An image taken at an angle: 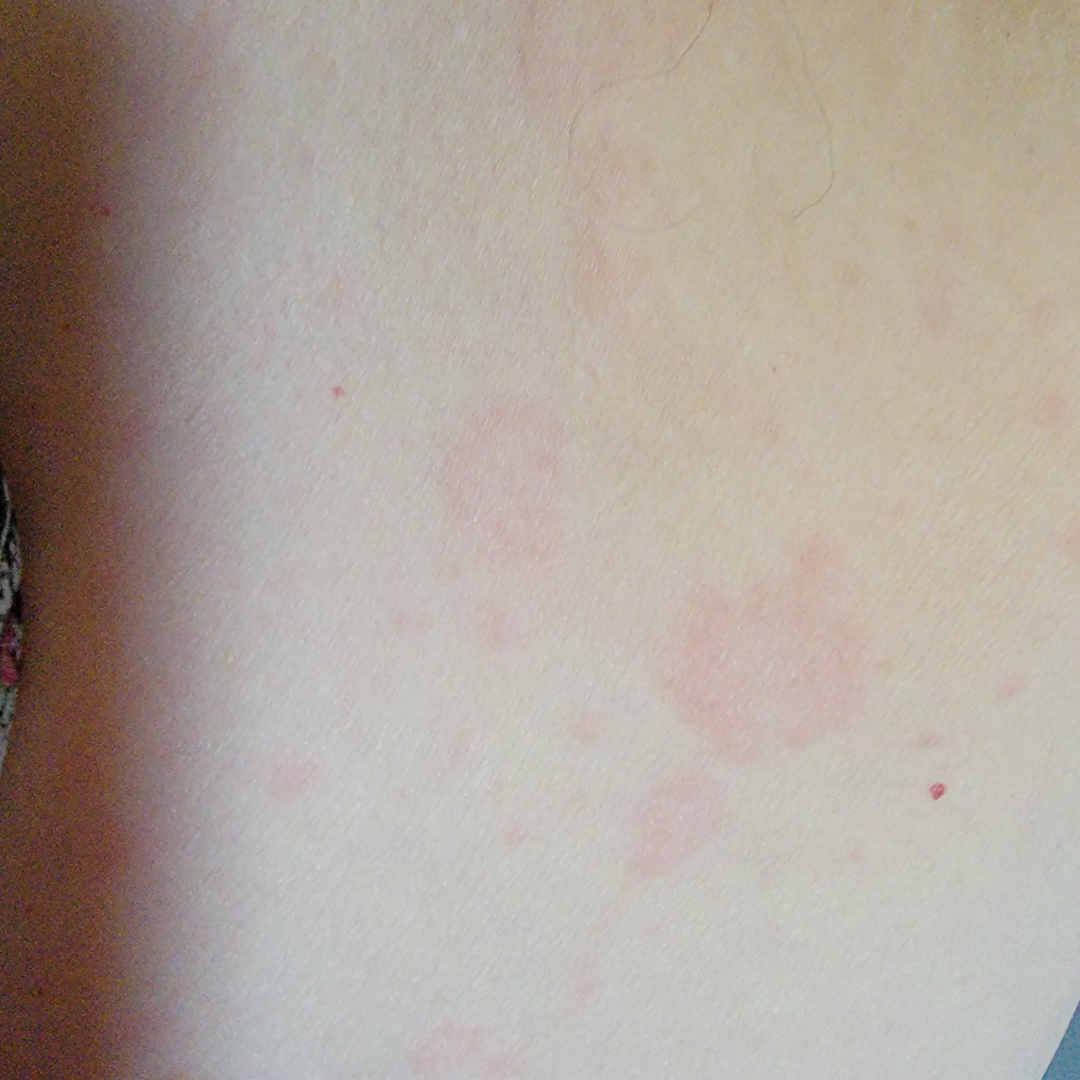The case was difficult to assess from the available photograph.